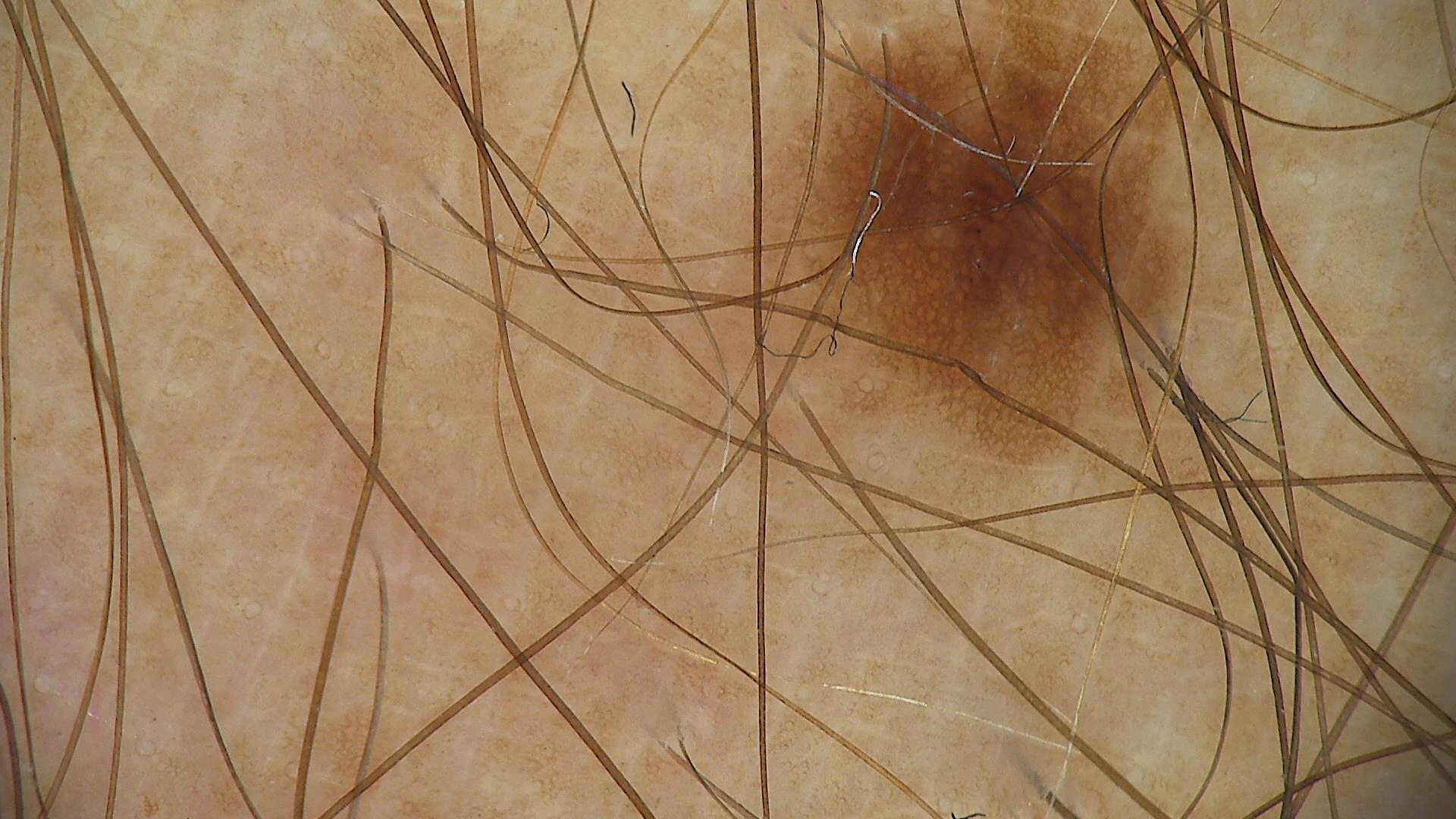modality: dermatoscopy; label: dysplastic junctional nevus (expert consensus).